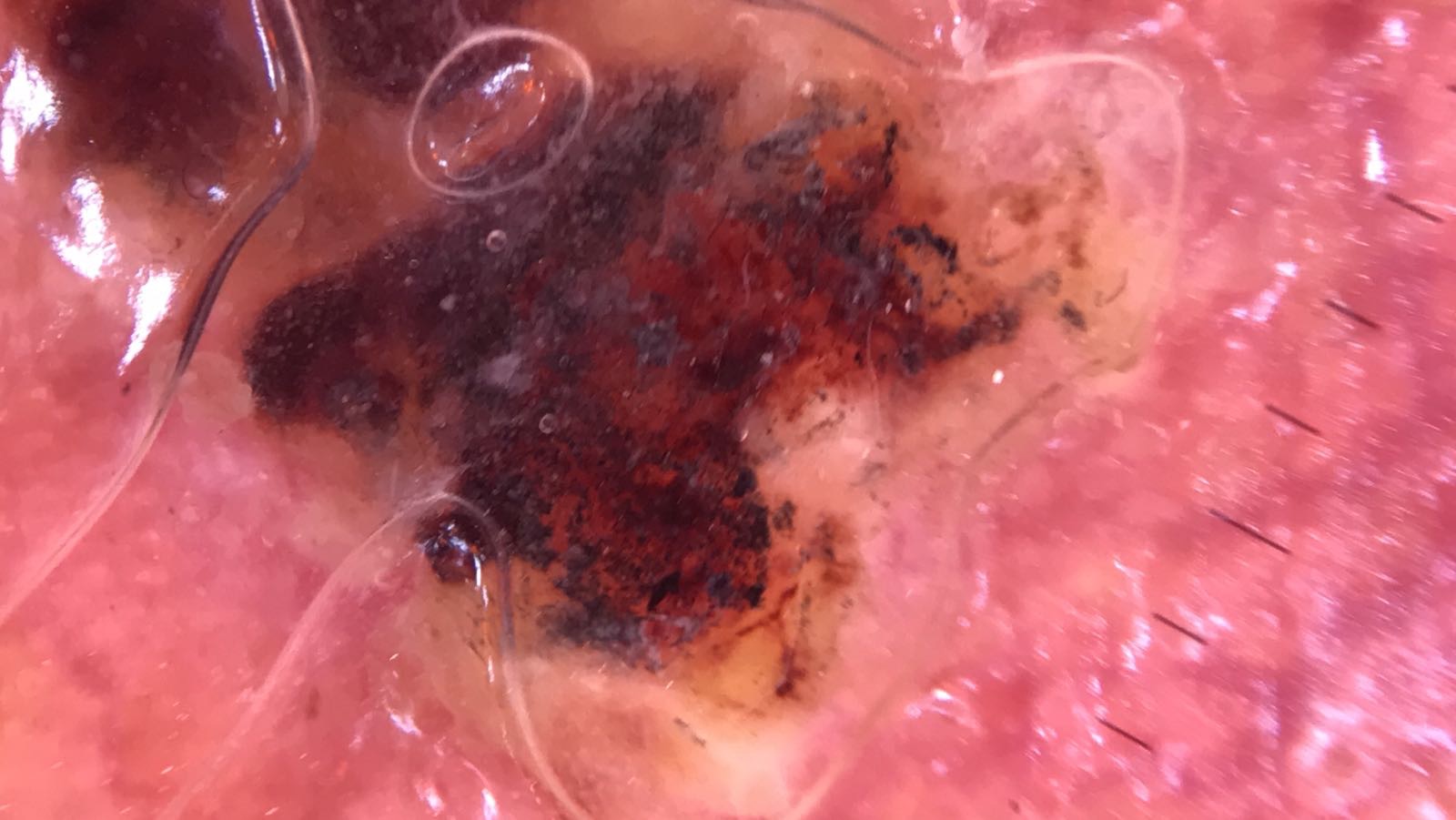| key | value |
|---|---|
| lesion type | keratinocytic |
| diagnostic label | squamous cell carcinoma (biopsy-proven) |